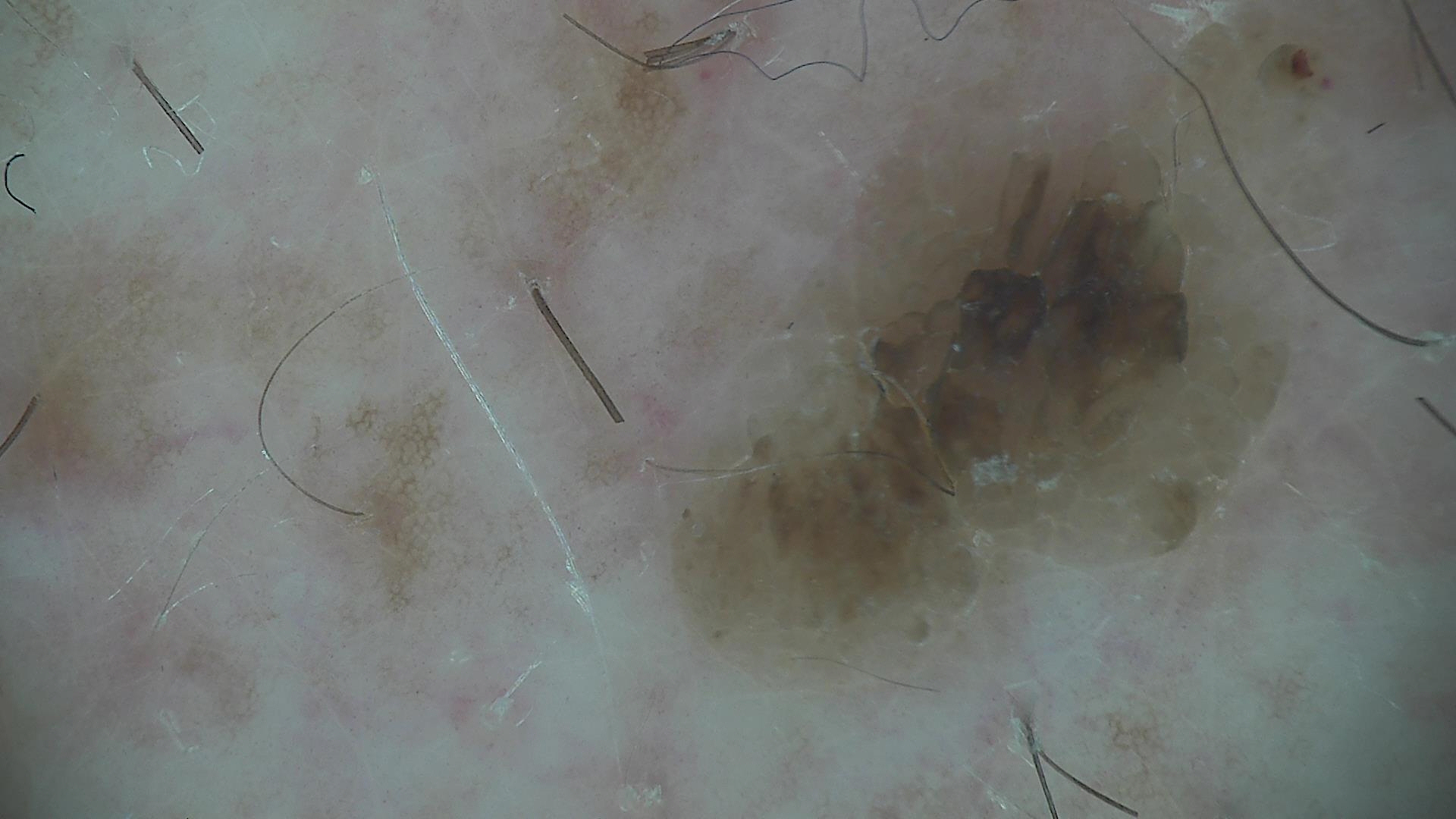class=seborrheic keratosis (expert consensus)